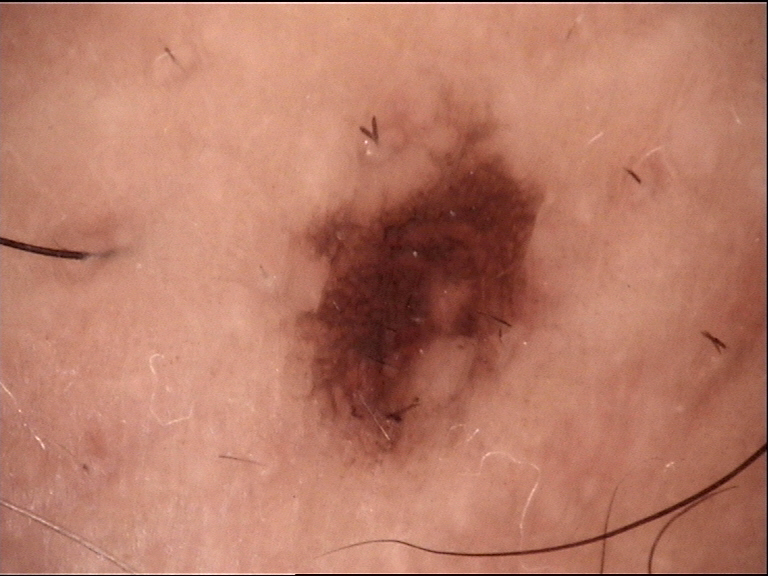Q: What kind of lesion is this?
A: banal
Q: What is this lesion?
A: compound nevus (expert consensus)